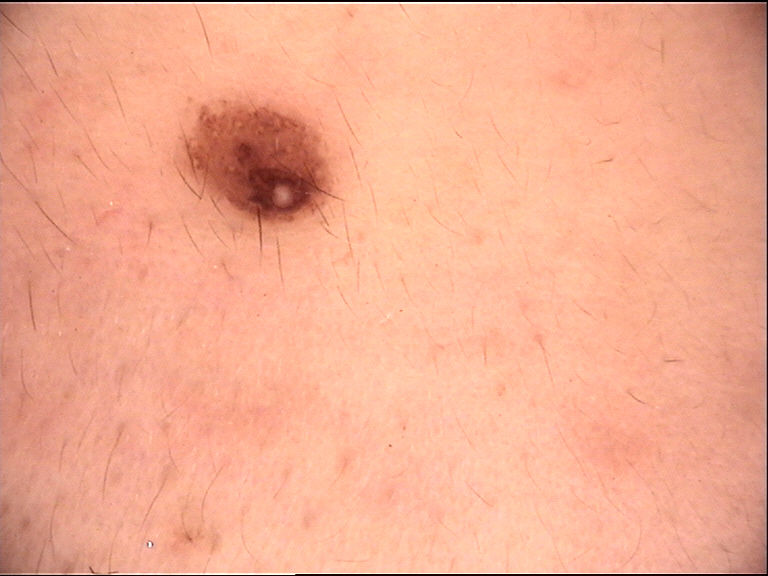Findings: A skin lesion imaged with a dermatoscope. Impression: Diagnosed as a compound nevus.